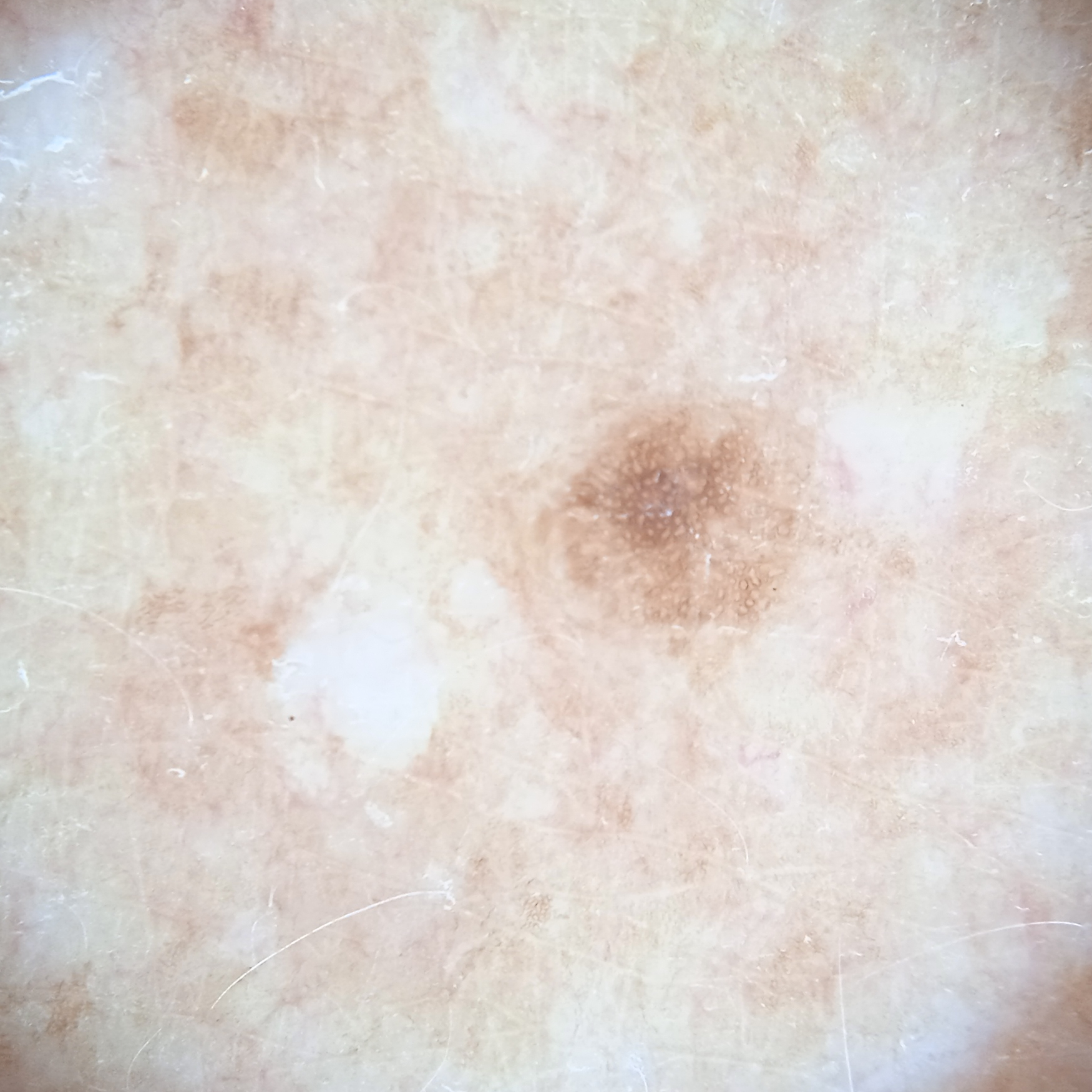Findings:
* sun reaction: skin tans without first burning
* referral context: research study (no referral diagnosis)
* image type: dermatoscopic image
* patient: female, age 75
* location: the back
* diagnosis: melanocytic nevus (dermatologist consensus)